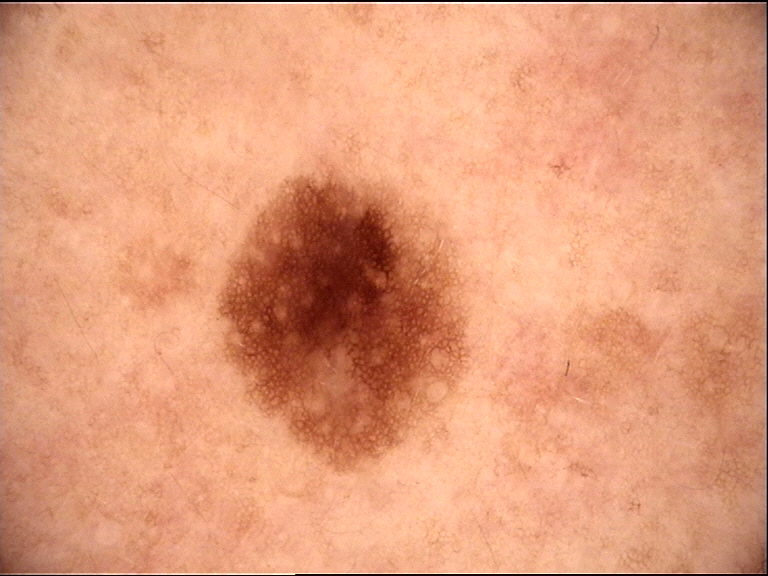The diagnosis was a benign lesion — a dysplastic junctional nevus.